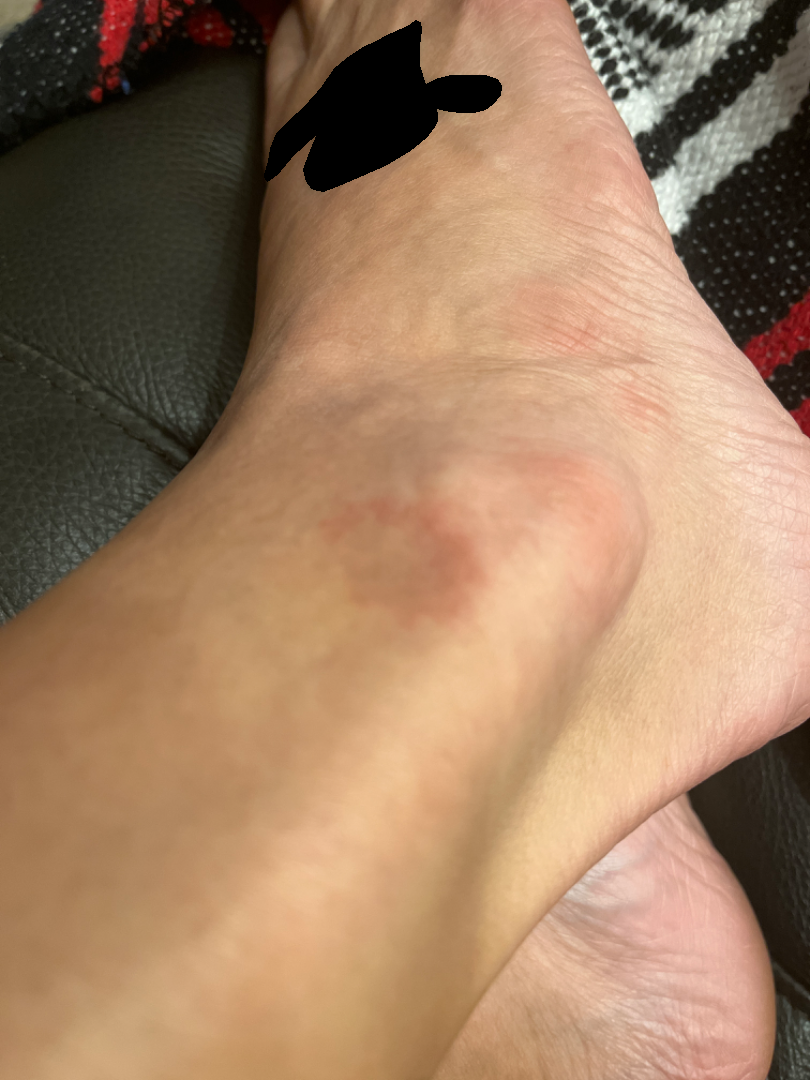Q: What is the patient's skin tone?
A: Fitzpatrick III; non-clinician graders estimated Monk Skin Tone 2 or 3
Q: How does the patient describe it?
A: skin that appeared healthy to them
Q: Who is the patient?
A: female
Q: How was the photo taken?
A: at an angle
Q: Constitutional symptoms?
A: none reported
Q: How does the lesion feel?
A: flat
Q: Reported symptoms?
A: bothersome appearance, darkening and enlargement
Q: Where on the body?
A: top or side of the foot
Q: What conditions are considered?
A: single-reviewer assessment: most consistent with Eczema; the differential also includes Pigmented purpuric eruption